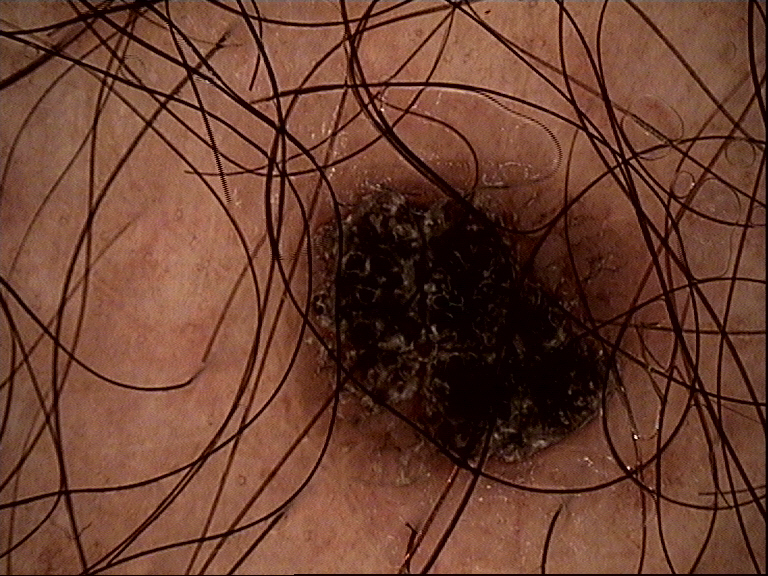Case:
* modality: dermoscopy
* label: seborrheic keratosis (expert consensus)